Texture is reported as rough or flaky · reported lesion symptoms include bothersome appearance, itching and enlargement · reported duration is more than one year · an image taken at an angle · the lesion involves the arm — 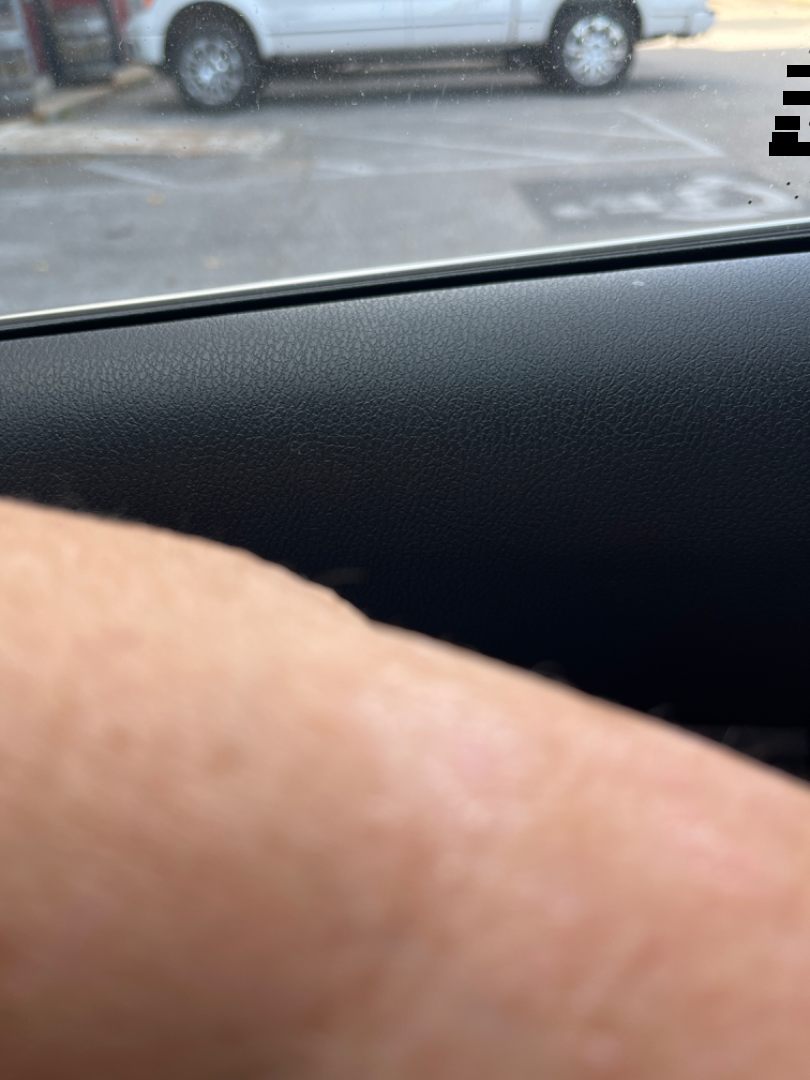<report>
  <differential>
    <leading>Eczema</leading>
  </differential>
</report>